A dermoscopic close-up of a skin lesion. A female subject, aged 8 to 12 — 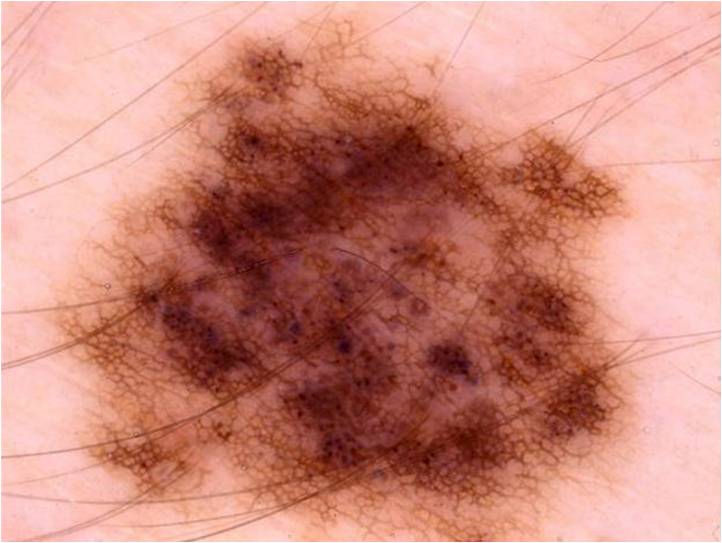| field | value |
|---|---|
| dermoscopic findings | pigment network and globules; absent: streaks, negative network, and milia-like cysts |
| size | ~60% of the field |
| bounding box | box(41, 10, 639, 541) |
| diagnostic label | a melanocytic nevus, a benign lesion |